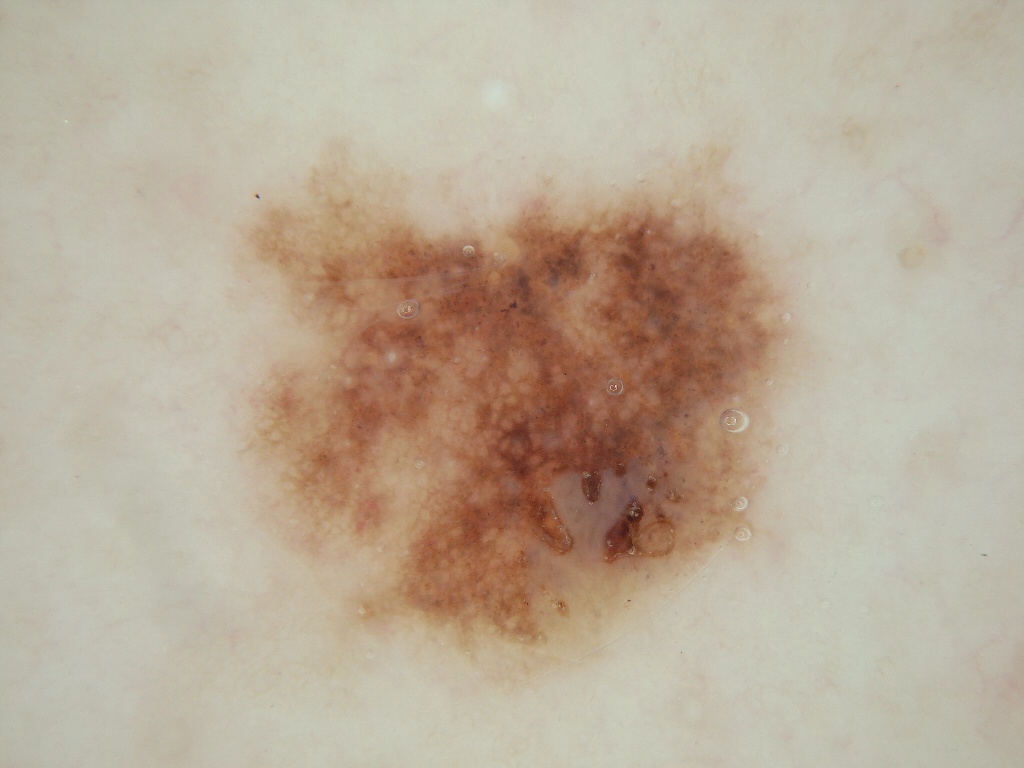Image and clinical context:
Dermoscopy of a skin lesion. A female subject in their mid-60s. The lesion occupies roughly 28% of the field. Dermoscopic review identifies milia-like cysts, globules, and pigment network; no streaks or negative network. In (x1, y1, x2, y2) order, the lesion is located at <box>235, 145, 796, 684</box>.
Assessment:
Diagnosed as a melanocytic nevus.